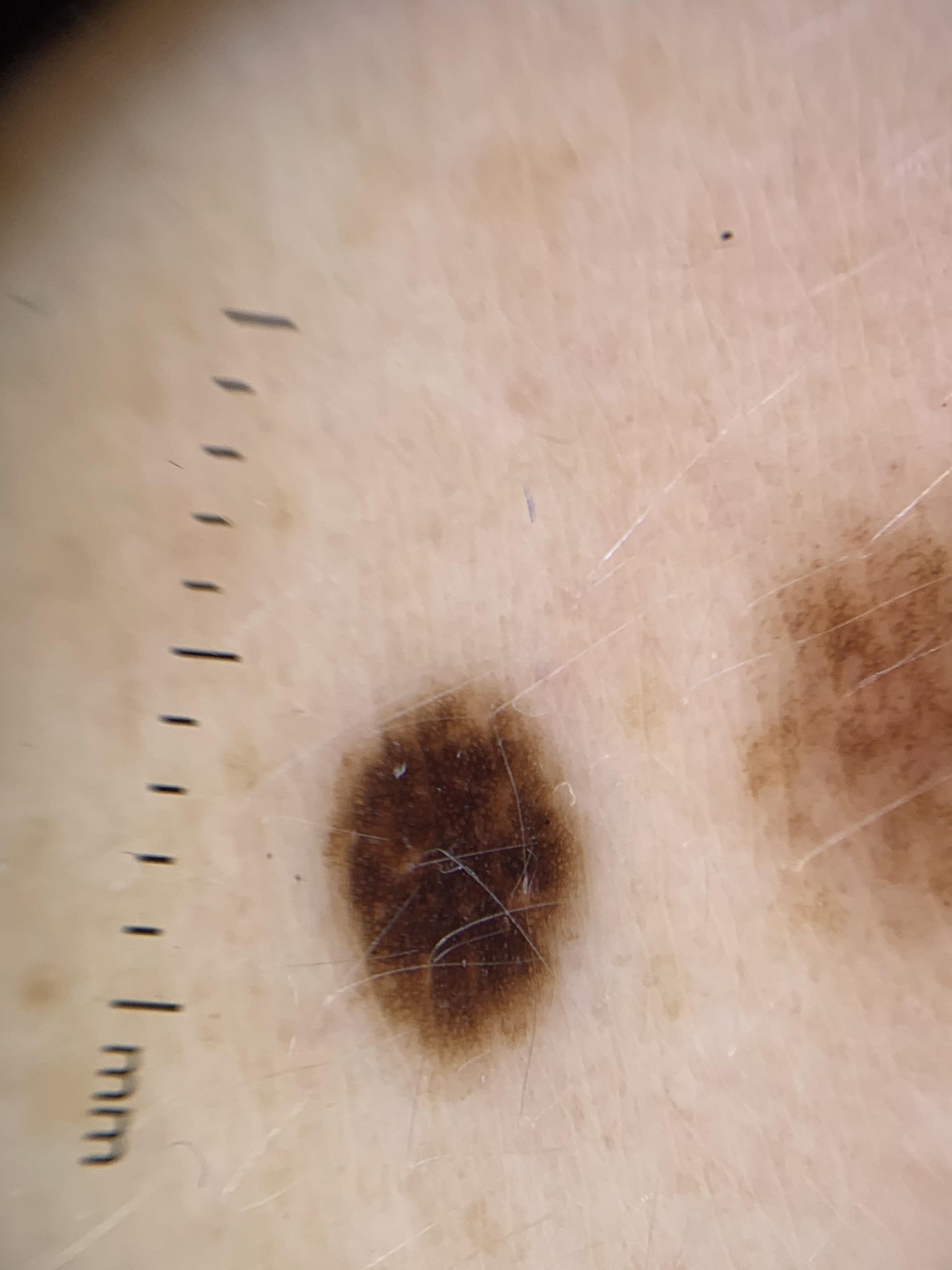modality: contact-polarized dermoscopy | patient: female, aged approximately 40 | location: the trunk, specifically the posterior trunk | pathology: Nevus (biopsy-proven).